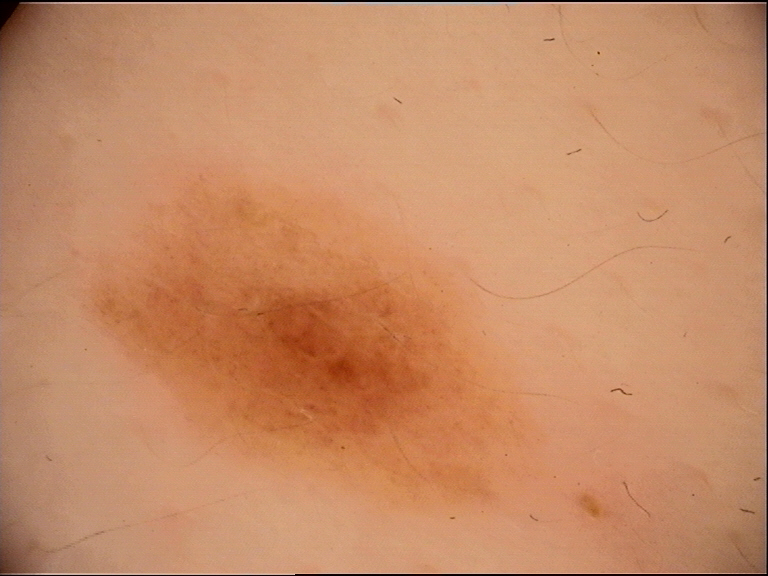Findings: A dermoscopic photograph of a skin lesion. This is a banal lesion. Impression: The diagnostic label was a junctional nevus.